The lesion involves the leg. The patient considered this a rash. No relevant systemic symptoms. Present for about one day. Skin tone: Fitzpatrick IV. Reported lesion symptoms include pain and bothersome appearance. A close-up photograph — 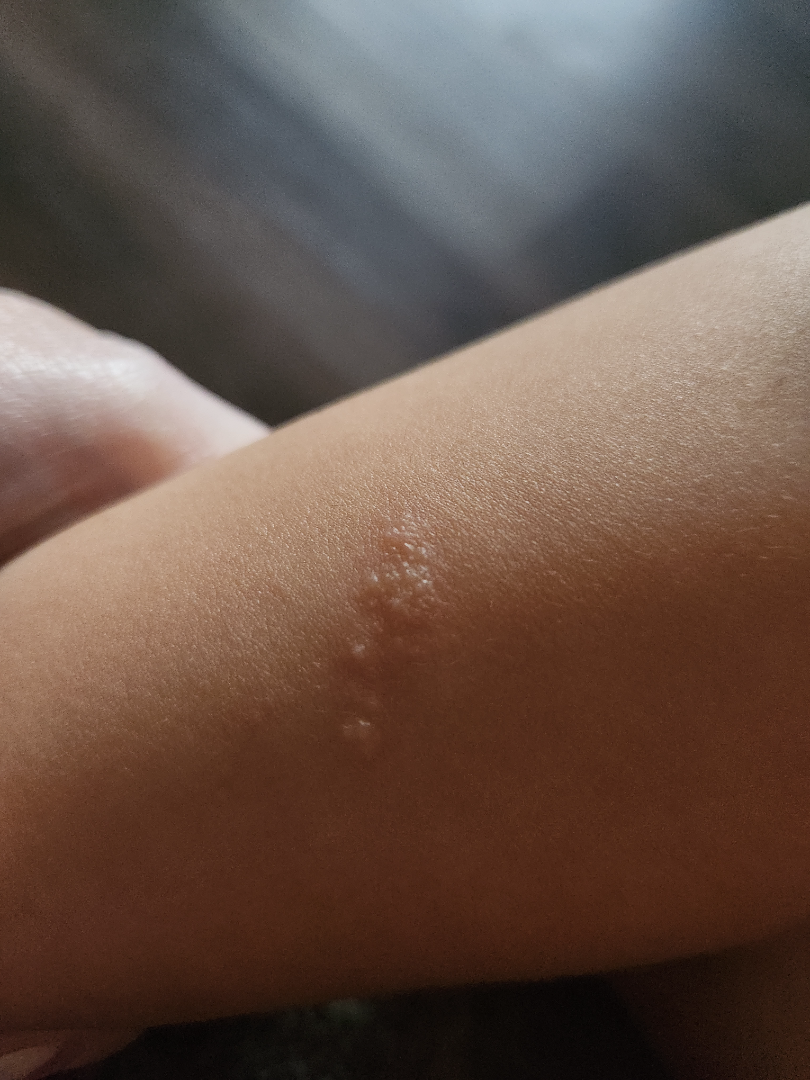{
  "assessment": "unable to determine"
}